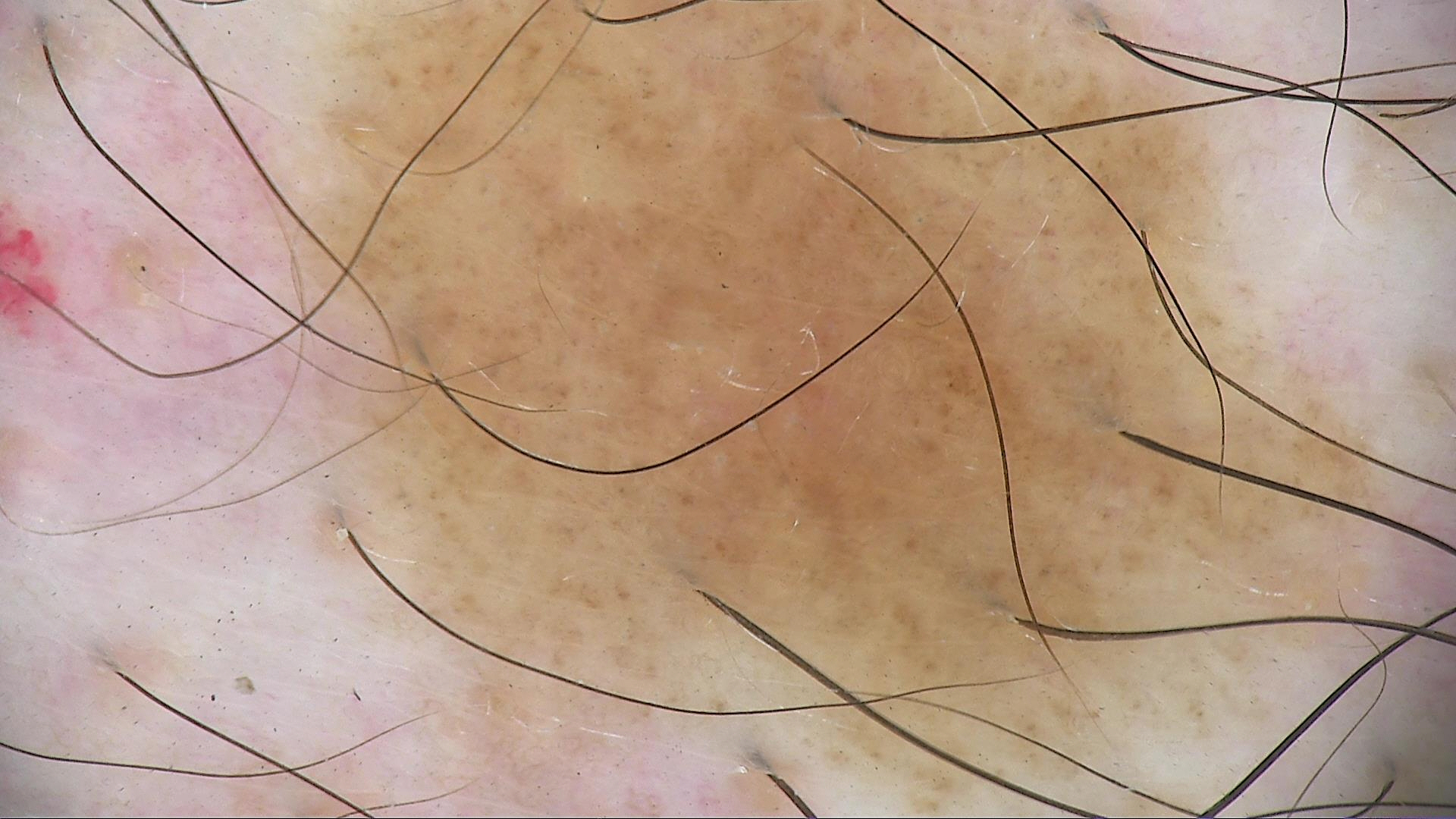  diagnosis:
    name: dysplastic junctional nevus
    code: jd
    malignancy: benign
    super_class: melanocytic
    confirmation: expert consensus